The subject is 40–49, female. Located on the back of the hand and arm. An image taken at an angle.
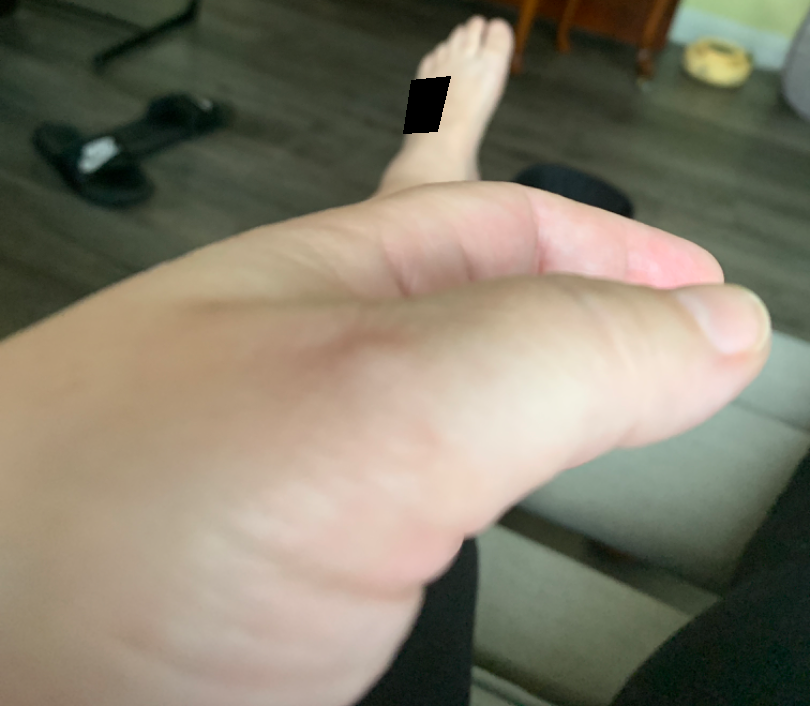Assessment:
No differential diagnosis could be assigned on photographic review.
Clinical context:
Reported duration is about one day. The lesion is associated with itching. Skin tone: self-reported Fitzpatrick phototype III. No associated systemic symptoms reported. Texture is reported as raised or bumpy.